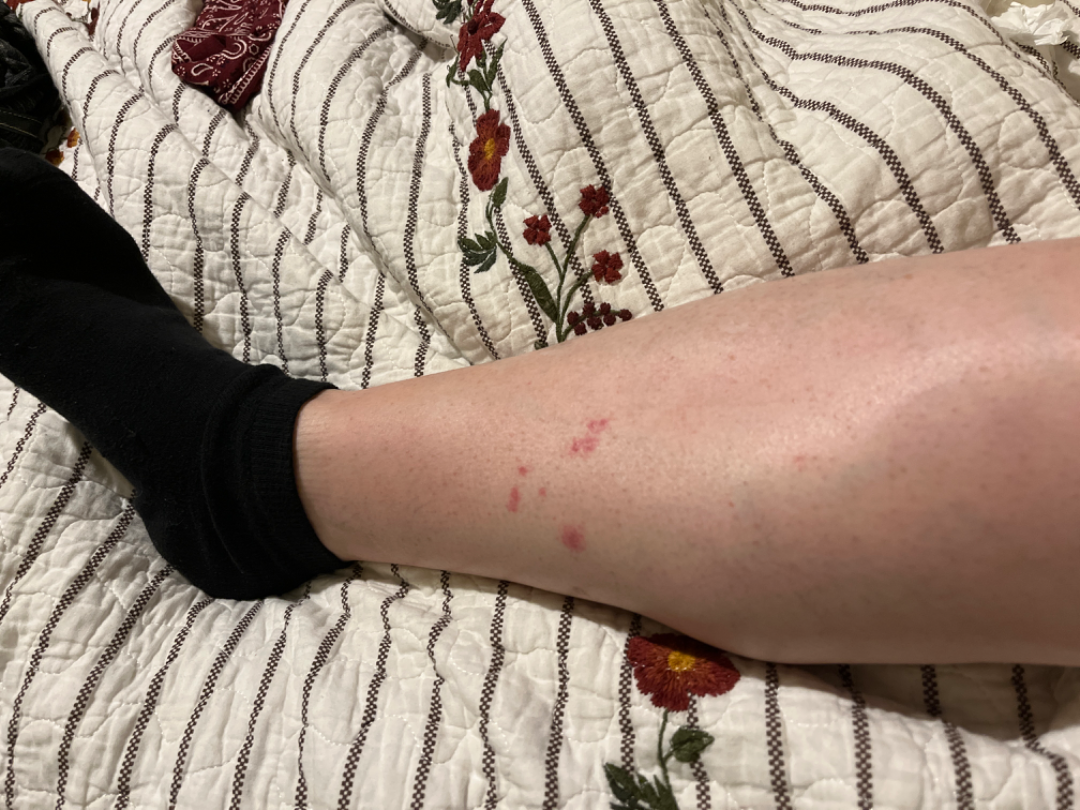<report>
  <patient>female, age 50–59</patient>
  <shot_type>at a distance</shot_type>
  <symptoms>none reported</symptoms>
  <systemic_symptoms>fatigue</systemic_symptoms>
  <texture>flat</texture>
  <body_site>leg</body_site>
  <patient_category>skin that appeared healthy to them</patient_category>
  <duration>less than one week</duration>
  <differential>
    <leading>Pigmented purpuric eruption</leading>
    <considered>Insect Bite</considered>
    <unlikely>Allergic Contact Dermatitis, Purpura</unlikely>
  </differential>
</report>